Dermoscopy of a skin lesion. A female subject aged around 50 — 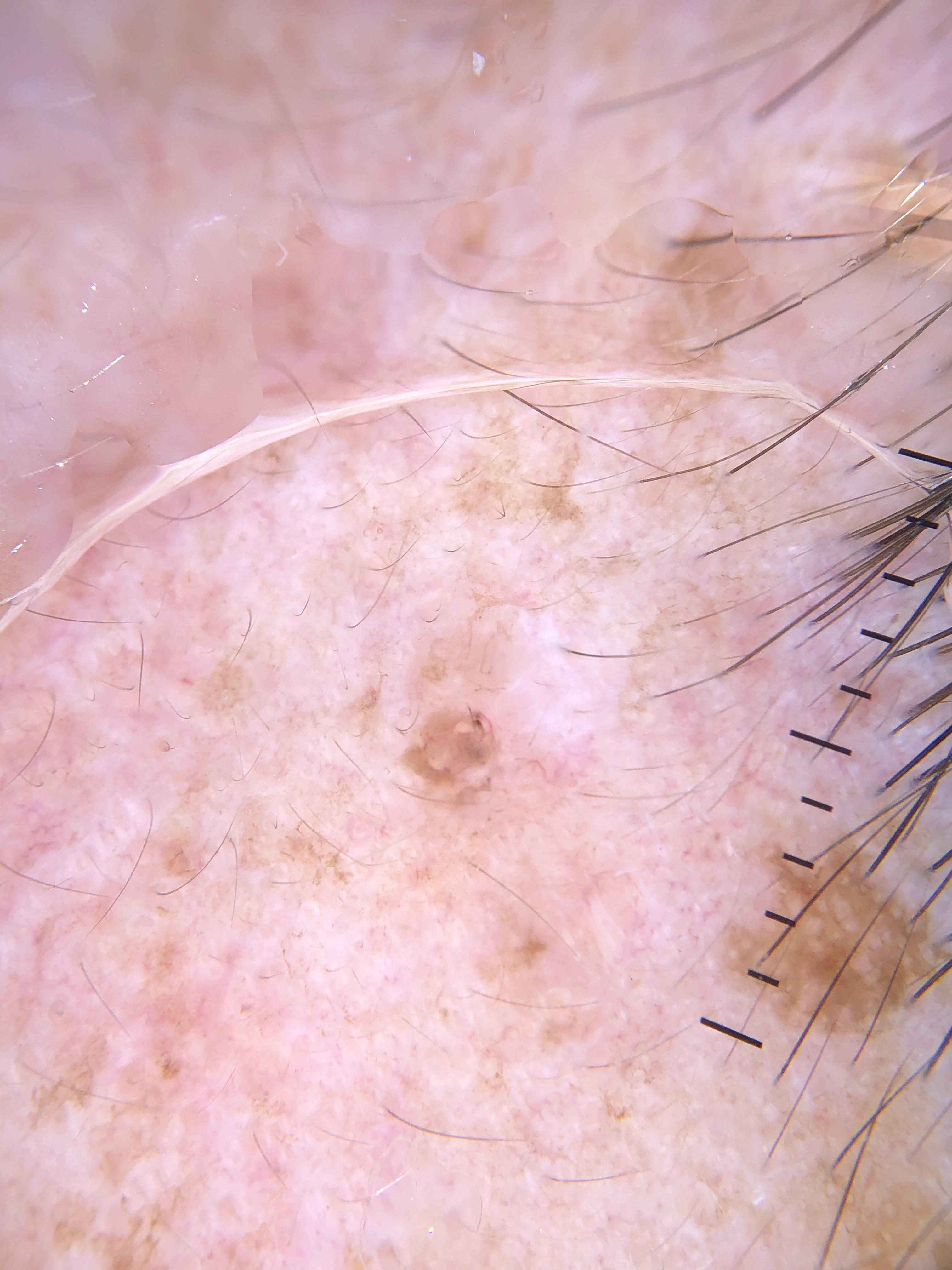site: the head or neck; diagnosis: Basal cell carcinoma (biopsy-proven).